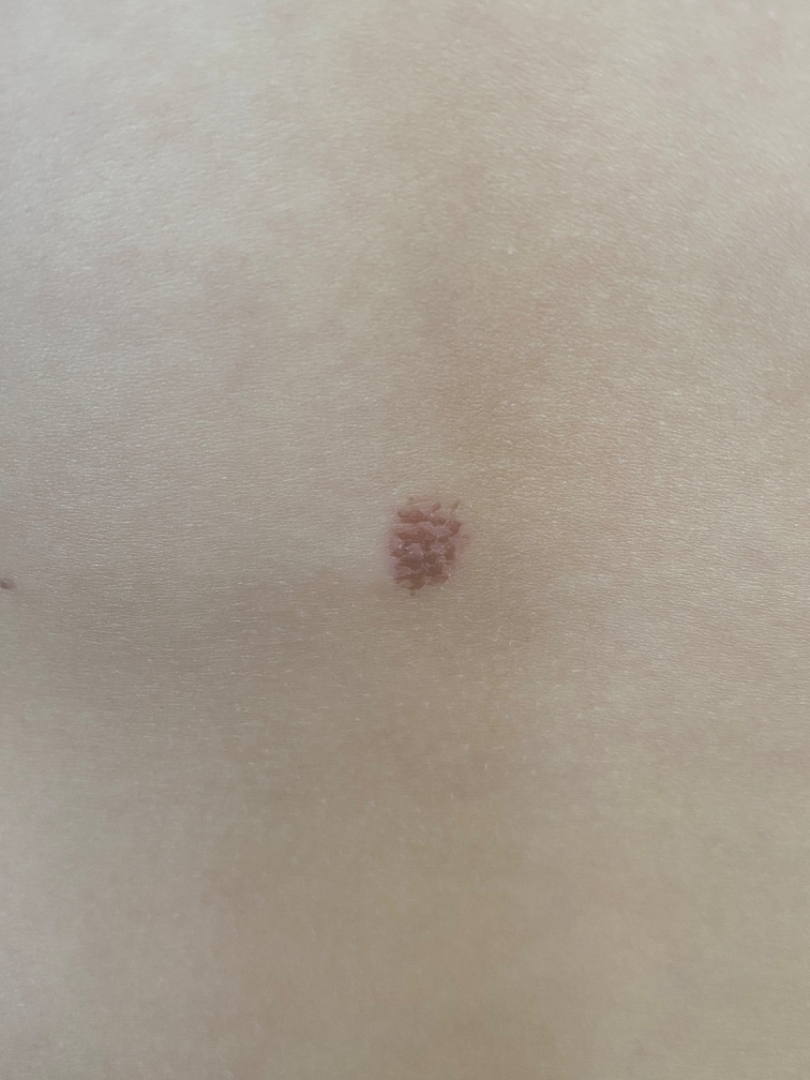The reviewer was unable to grade this case for skin condition.
The patient is a female aged 18–29.
The photograph is a close-up of the affected area.
The affected area is the back of the torso.